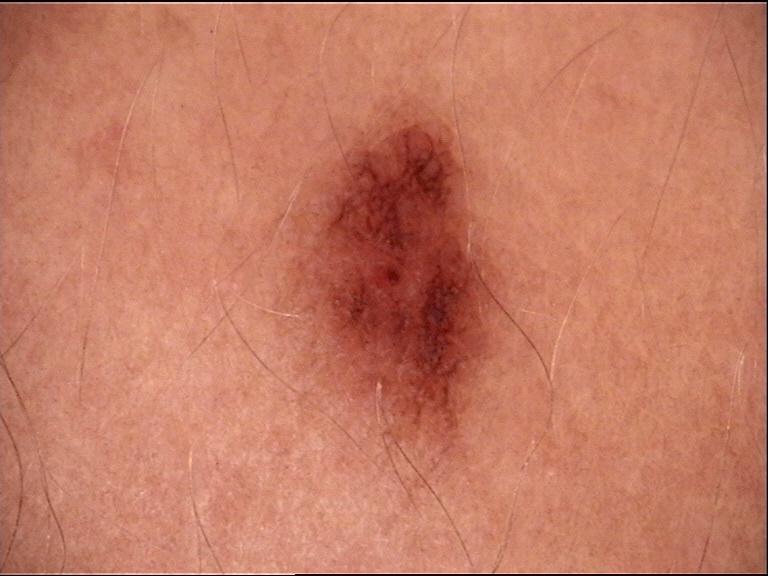Impression:
The diagnosis was a dysplastic junctional nevus.